This is a close-up image · male subject, age 30–39 · FST II · the lesion is associated with bothersome appearance and enlargement · the contributor reports the condition has been present for less than one week · the contributor reports the lesion is raised or bumpy and fluid-filled: 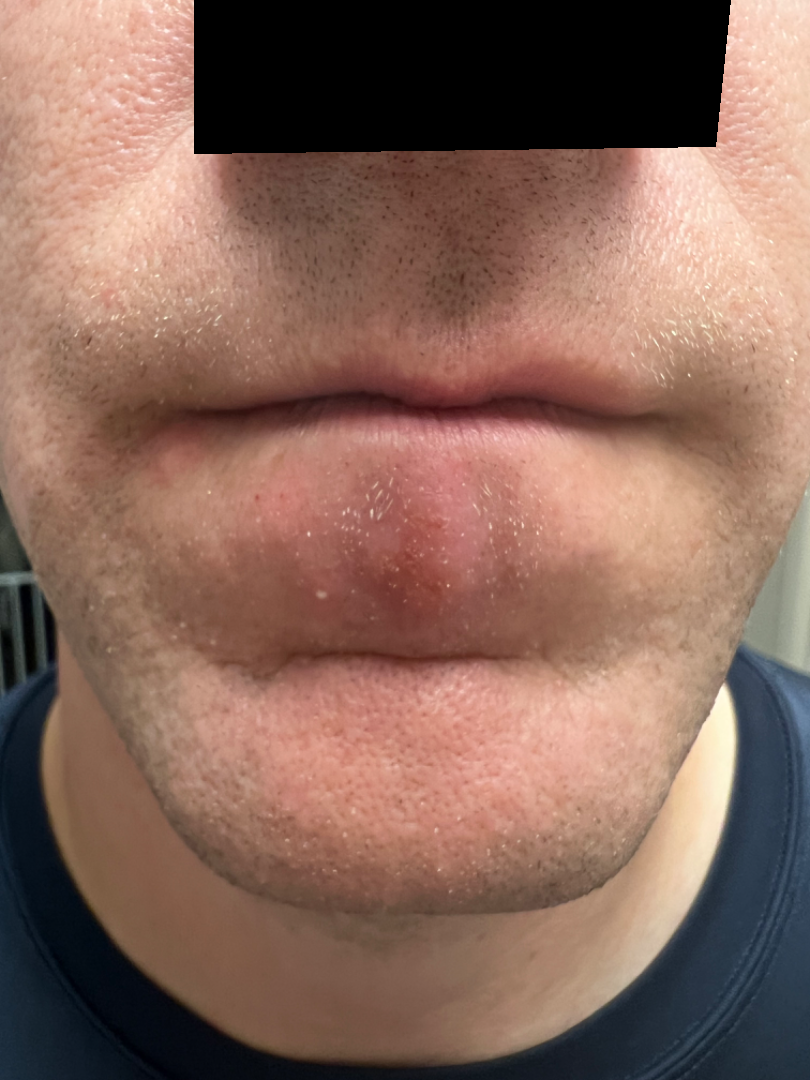differential = Irritant Contact Dermatitis (1.00)